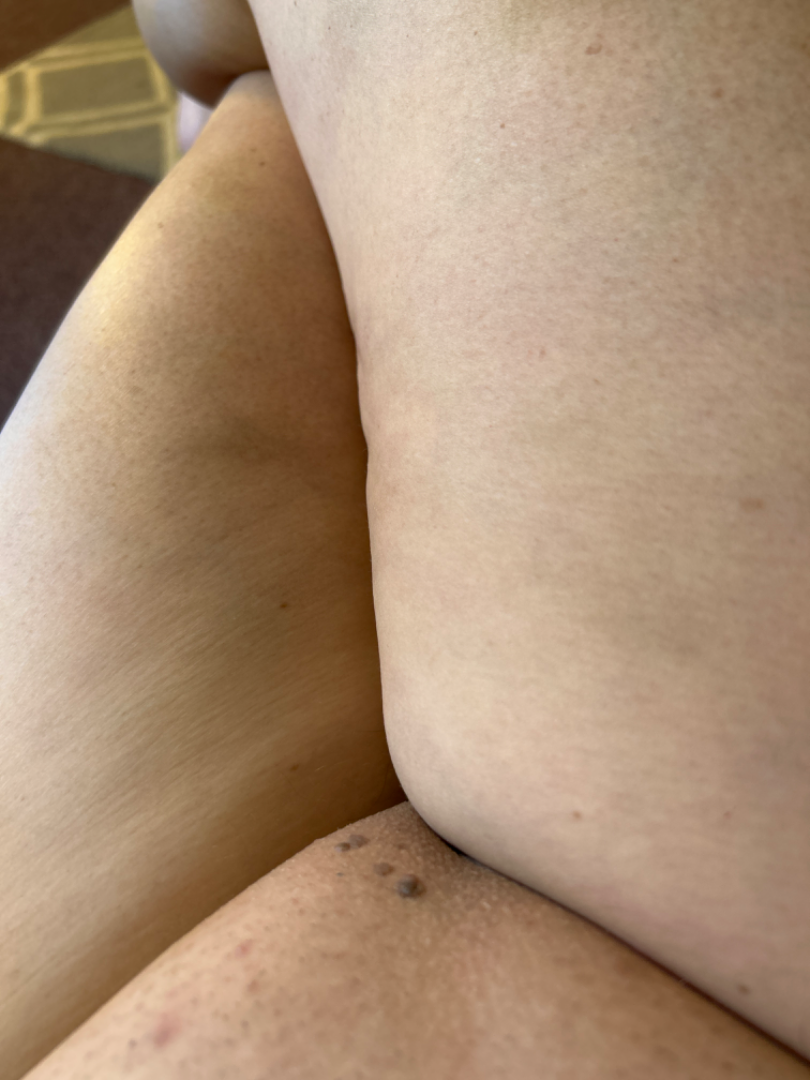framing: at a distance | differential: SK/ISK (possible); Condyloma acuminatum (possible).